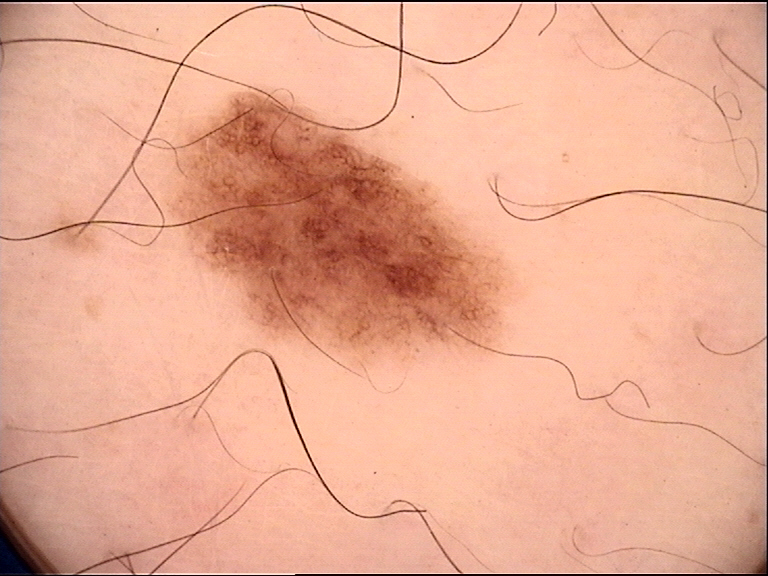diagnostic label = dysplastic junctional nevus (expert consensus).